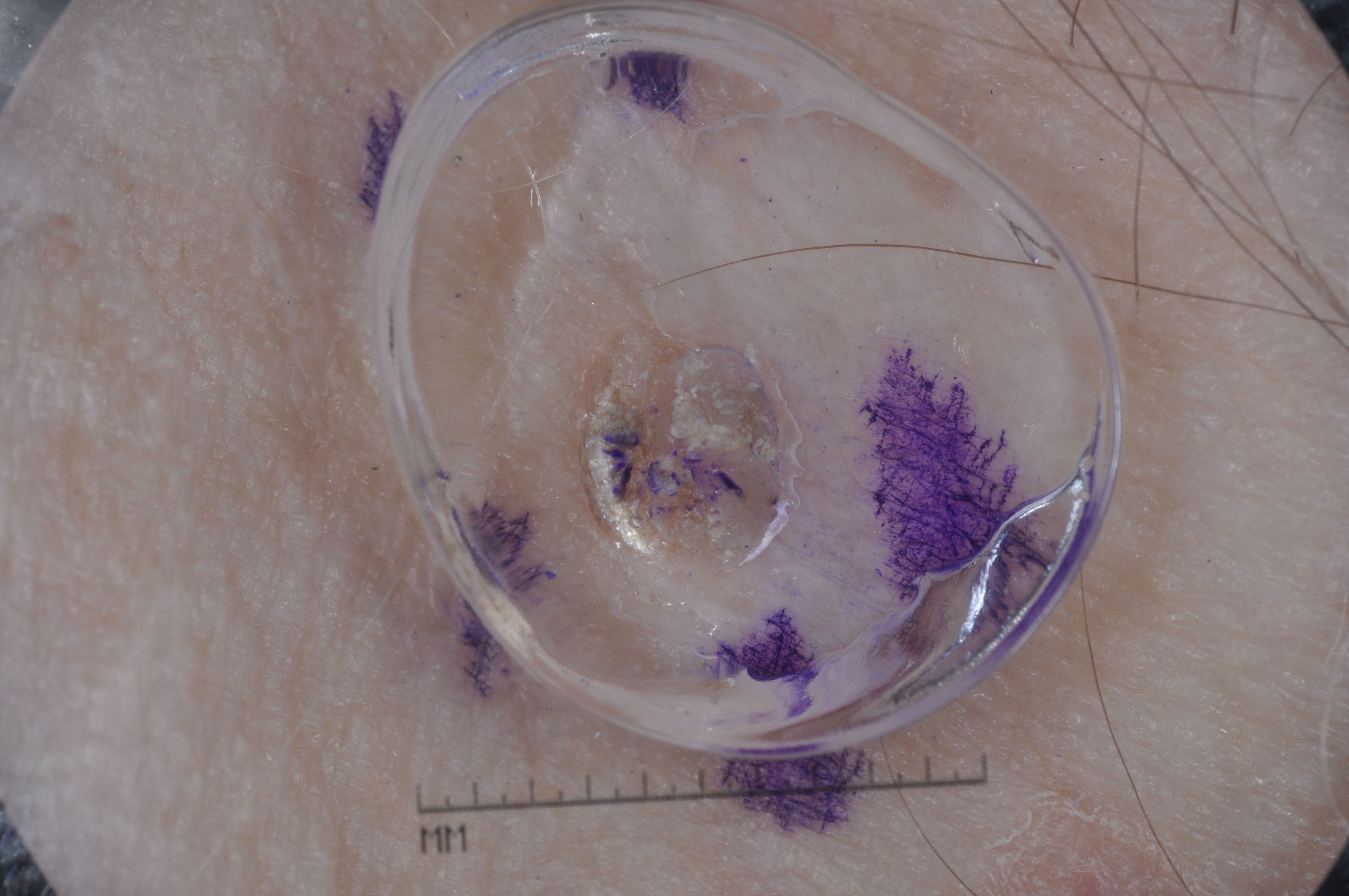patient: female, in their 80s | image type: dermoscopic image | bounding box: bbox(568, 321, 805, 589) | lesion extent: small | dermoscopic features not present: milia-like cysts, streaks, pigment network, and negative network | diagnostic label: a seborrheic keratosis, a benign skin lesion.